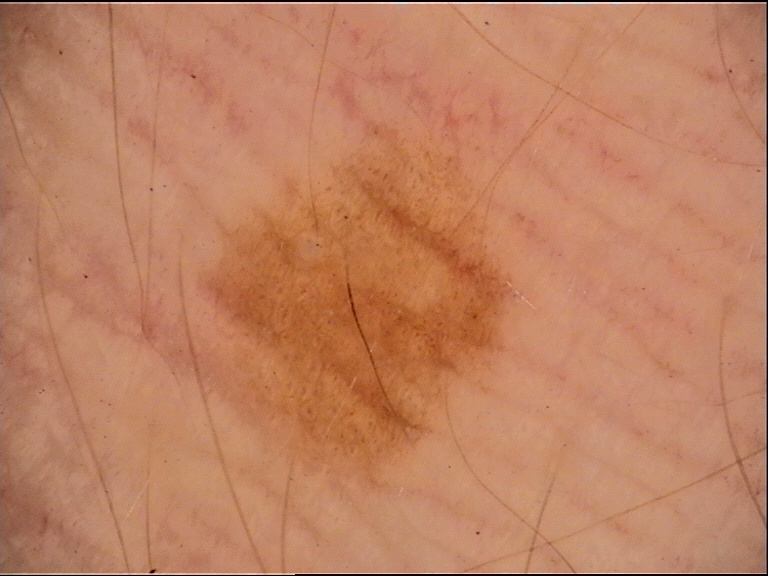imaging: dermatoscopy
diagnosis: acral junctional nevus (expert consensus)